A female patient aged 53-57 · a clinical overview photograph of a skin lesion — 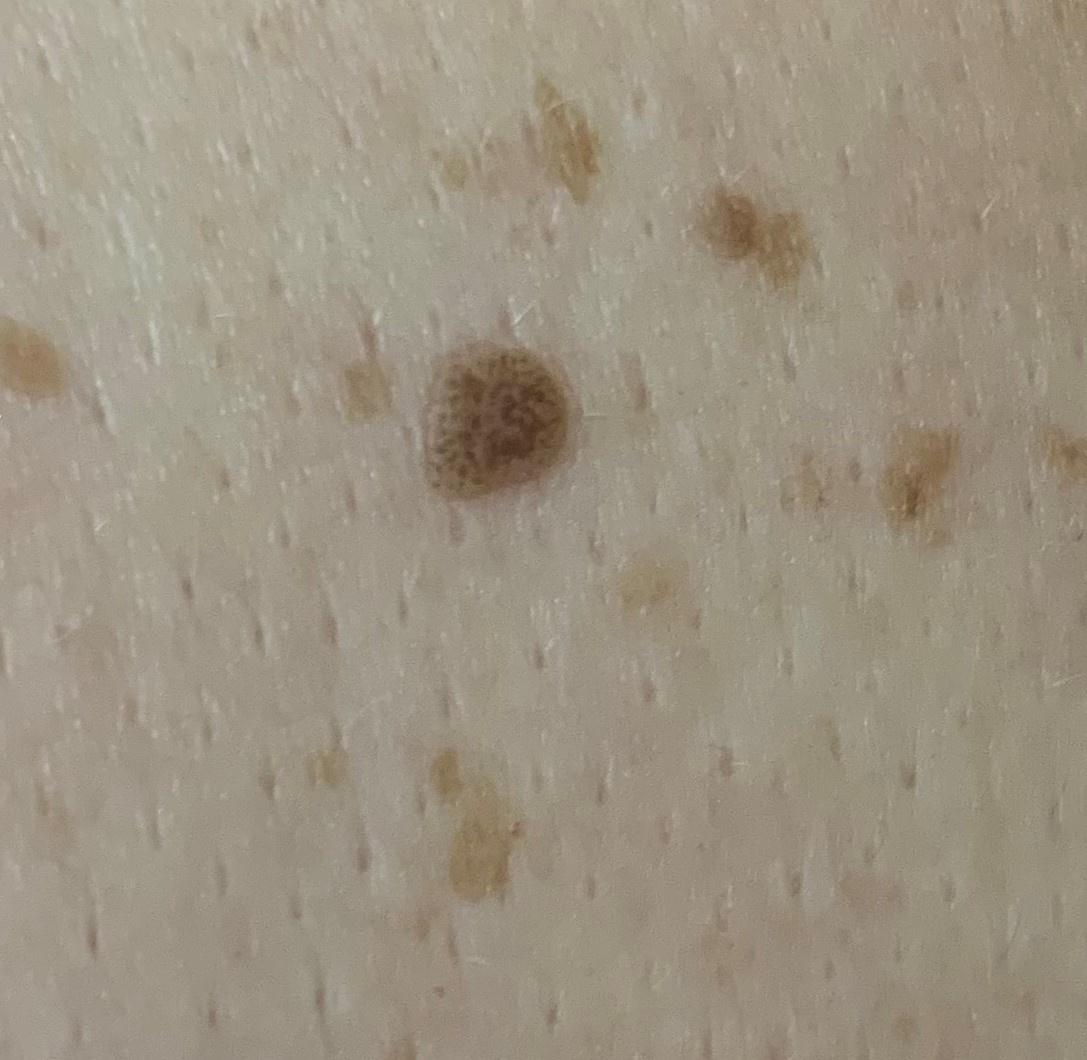- site: the trunk (the anterior trunk)
- impression: Seborrheic keratosis